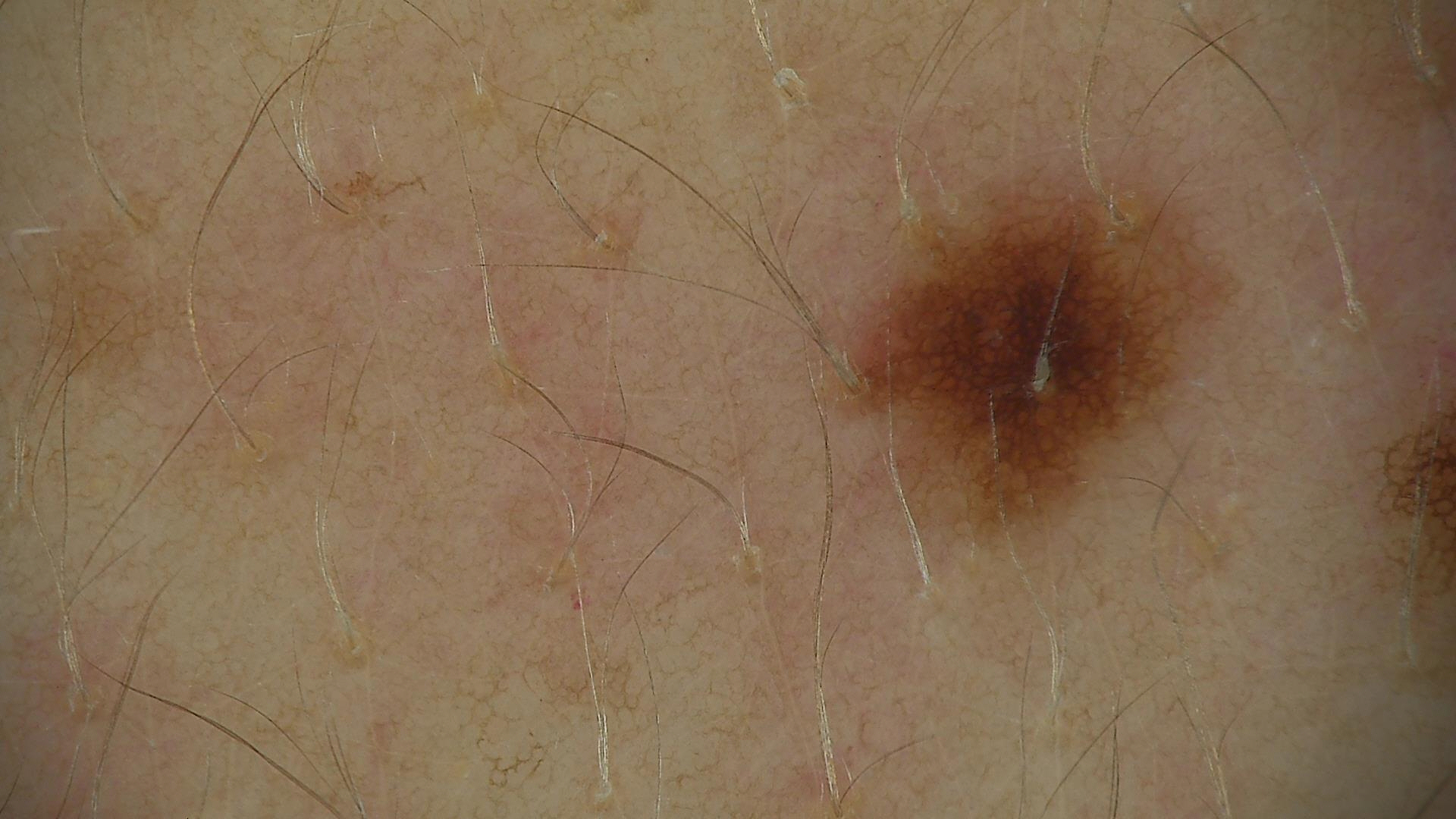A dermoscopic image of a skin lesion.
Consistent with a dysplastic junctional nevus.